A male subject, aged approximately 20; a dermatoscopic image of a skin lesion — 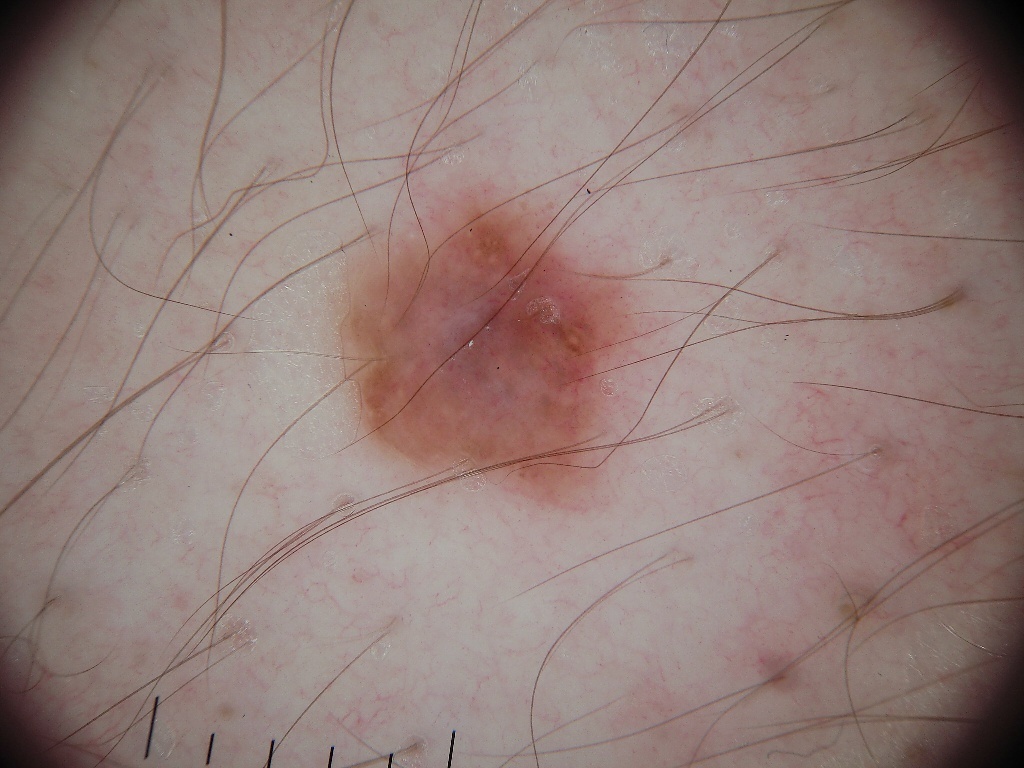Notes:
– absent dermoscopic features: globules, milia-like cysts, negative network, pigment network, and streaks
– lesion location: left=339, top=179, right=656, bottom=521
– diagnostic label: a melanocytic nevus, a benign lesion